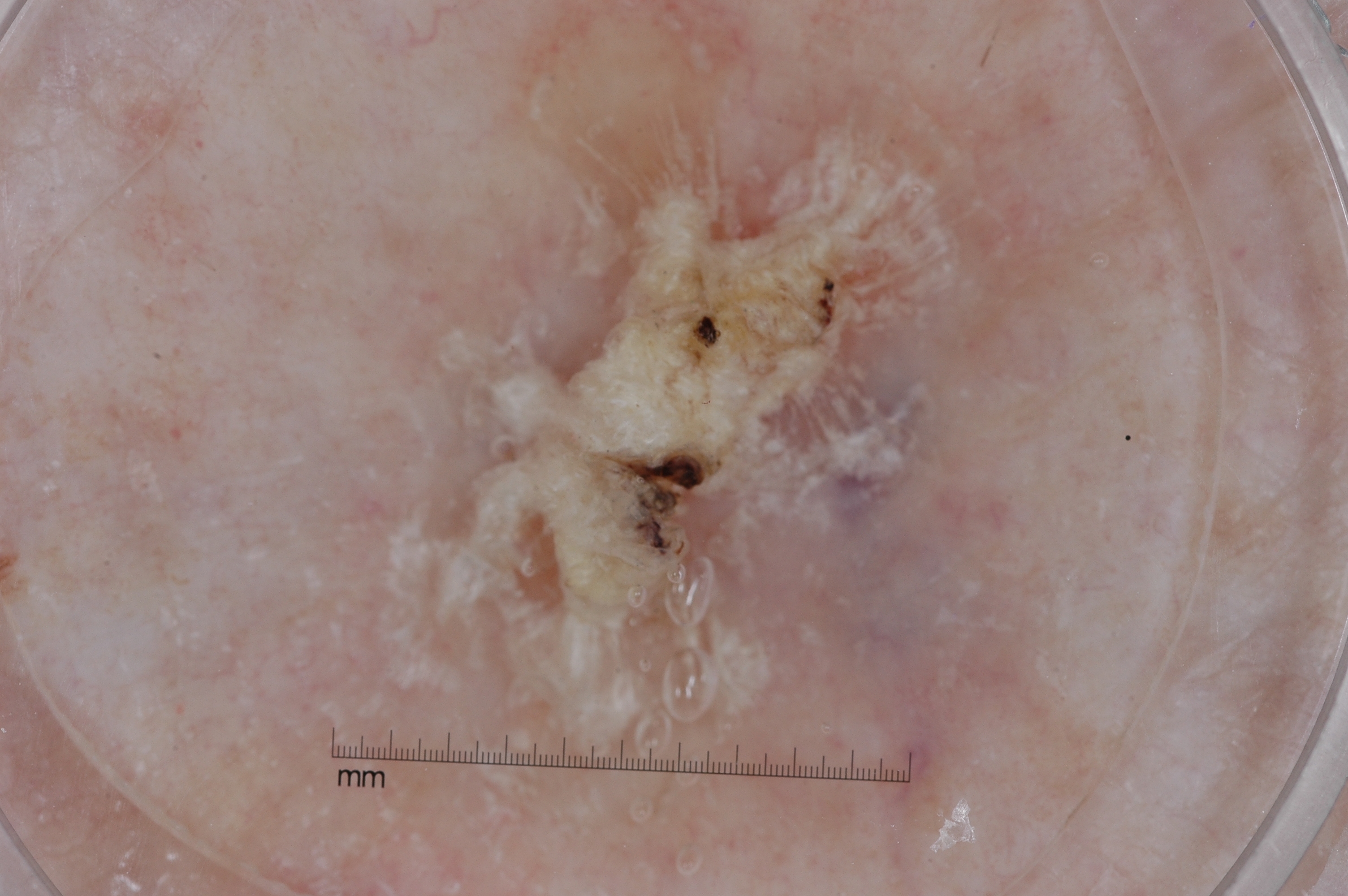Q: What are the patient's age and sex?
A: female, in their mid- to late 80s or older
Q: How was this image acquired?
A: dermoscopic image
Q: Which dermoscopic features are absent?
A: streaks, milia-like cysts, pigment network, and negative network
Q: How much of the field does the lesion occupy?
A: ~34% of the field
Q: Where is the lesion in the image?
A: [375,23,1076,816]
Q: What is the diagnosis?
A: a seborrheic keratosis